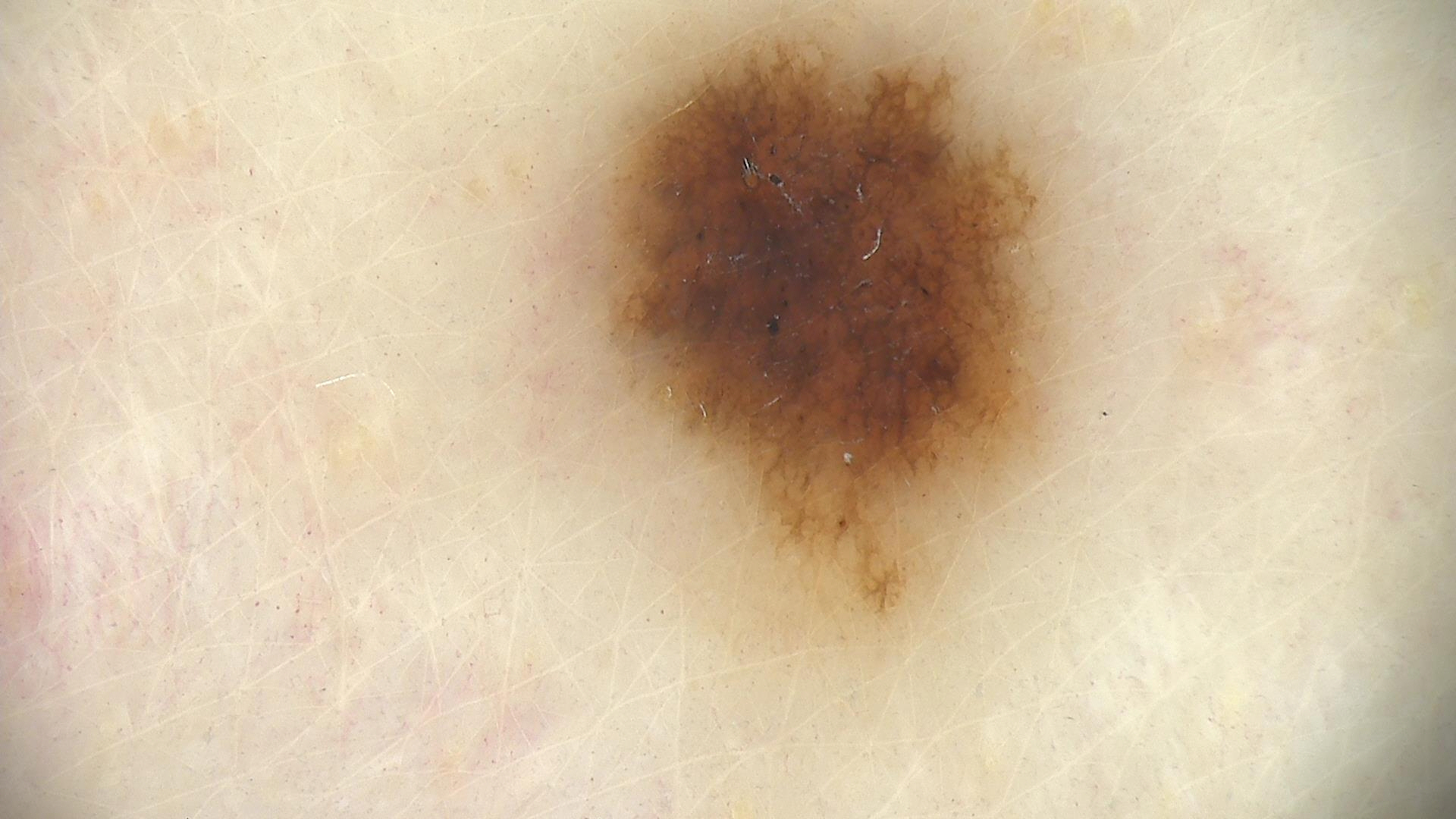A dermoscopic photograph of a skin lesion.
Labeled as a dysplastic junctional nevus.